A dermoscopic close-up of a skin lesion.
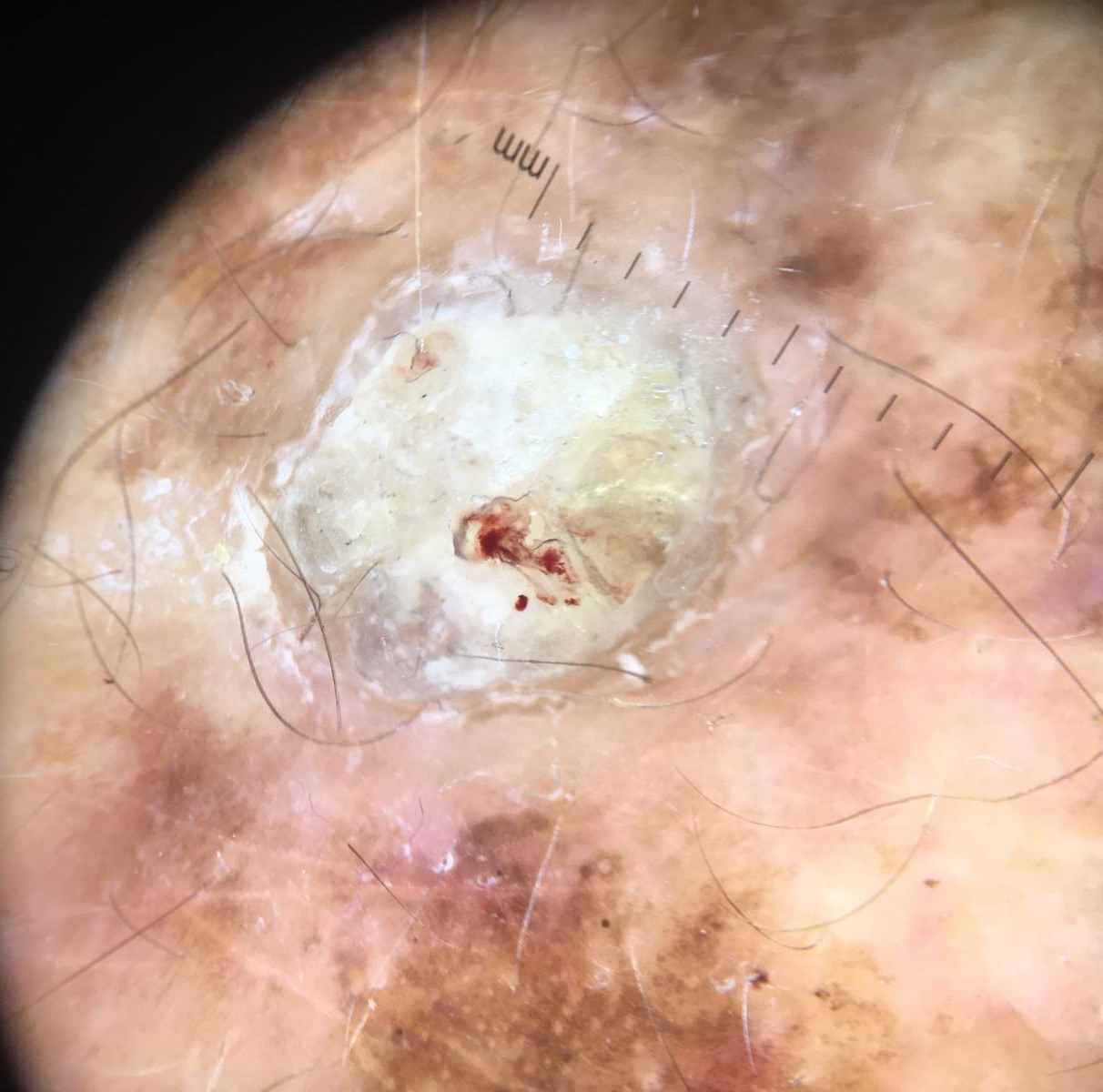Case:
* classification · keratinocytic
* pathology · squamous cell carcinoma (biopsy-proven)